A clinical photograph of a skin lesion · a patient aged 81 — 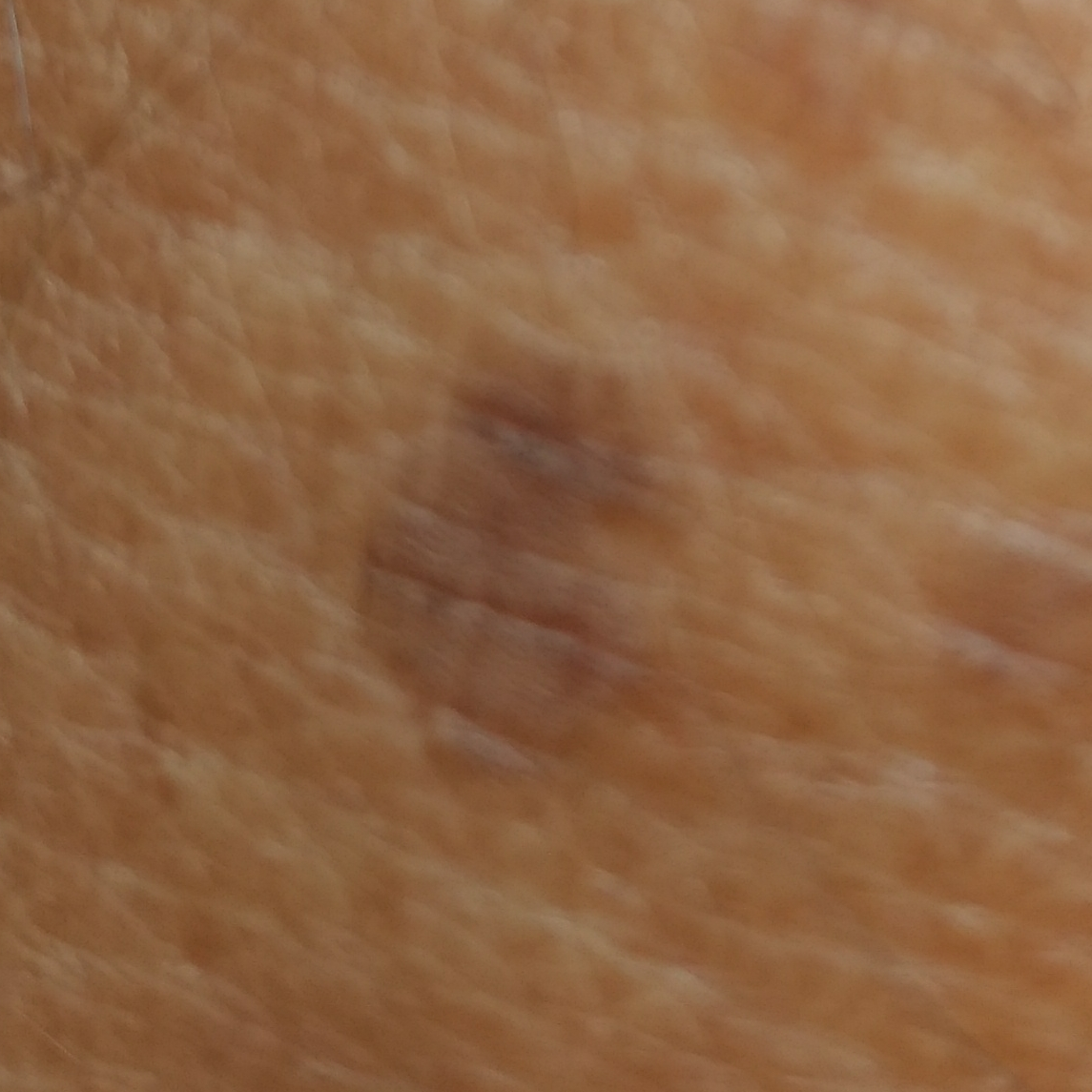Findings:
The lesion was found on an arm. The patient reports that the lesion is elevated and has grown, but has not changed.
Impression:
Clinically diagnosed as a seborrheic keratosis.